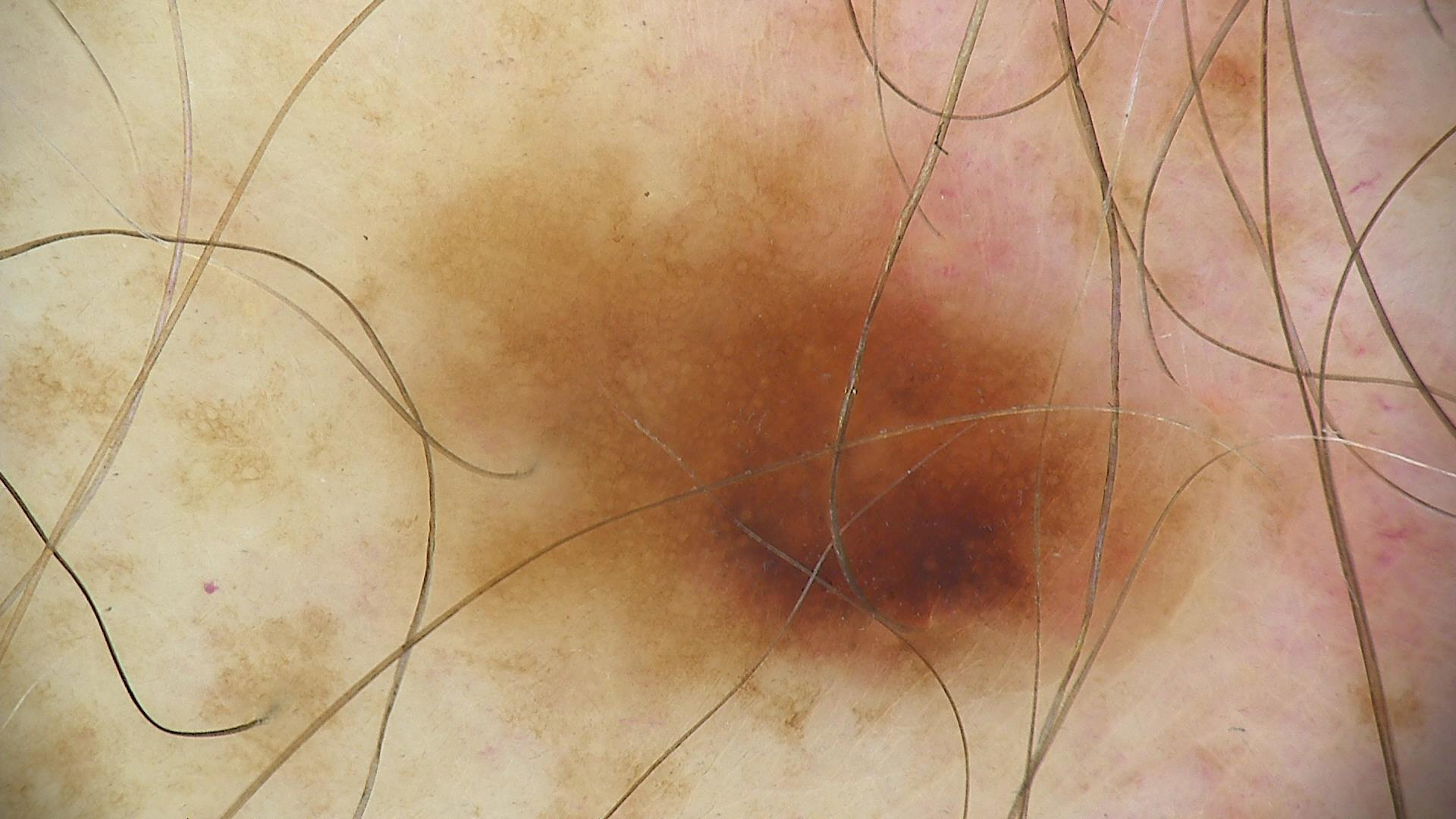Findings: A dermatoscopic image of a skin lesion. Conclusion: The diagnostic label was a dysplastic junctional nevus.